An image taken at a distance, the affected area is the leg.
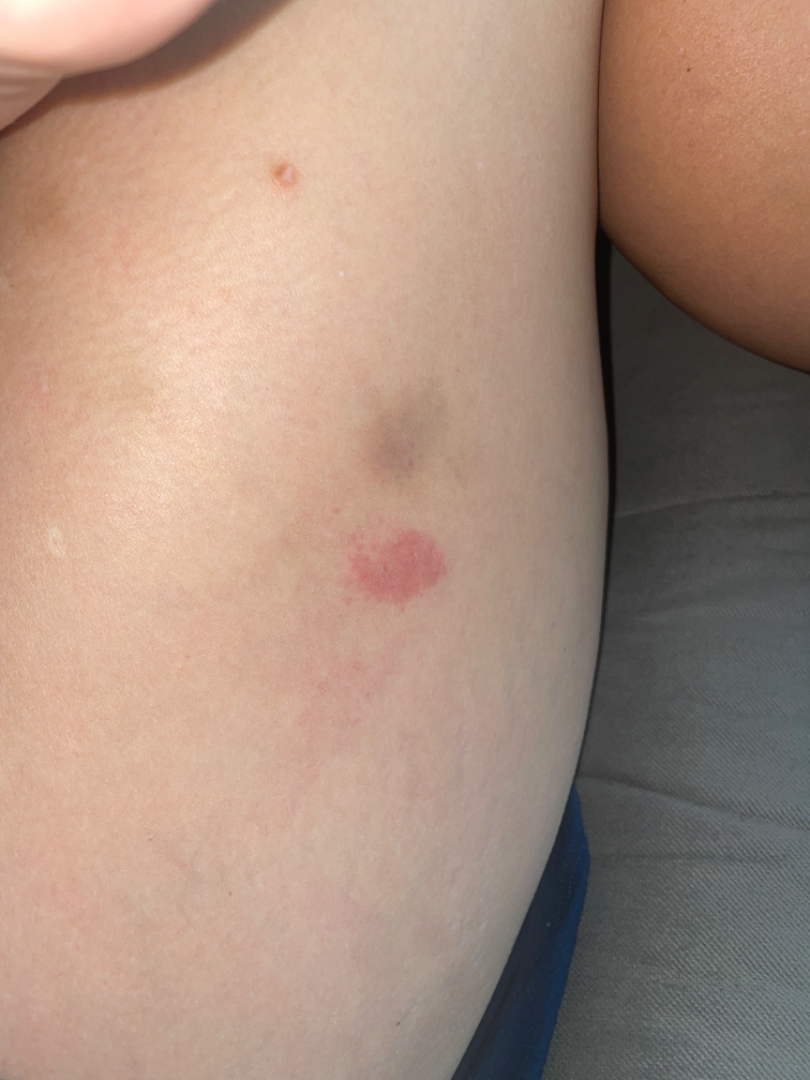Findings:
• assessment: indeterminate from the photograph